The patient reports a family history of skin cancer, immunosuppression, and a personal history of skin cancer. The patient says their skin reddens painfully with sun exposure: 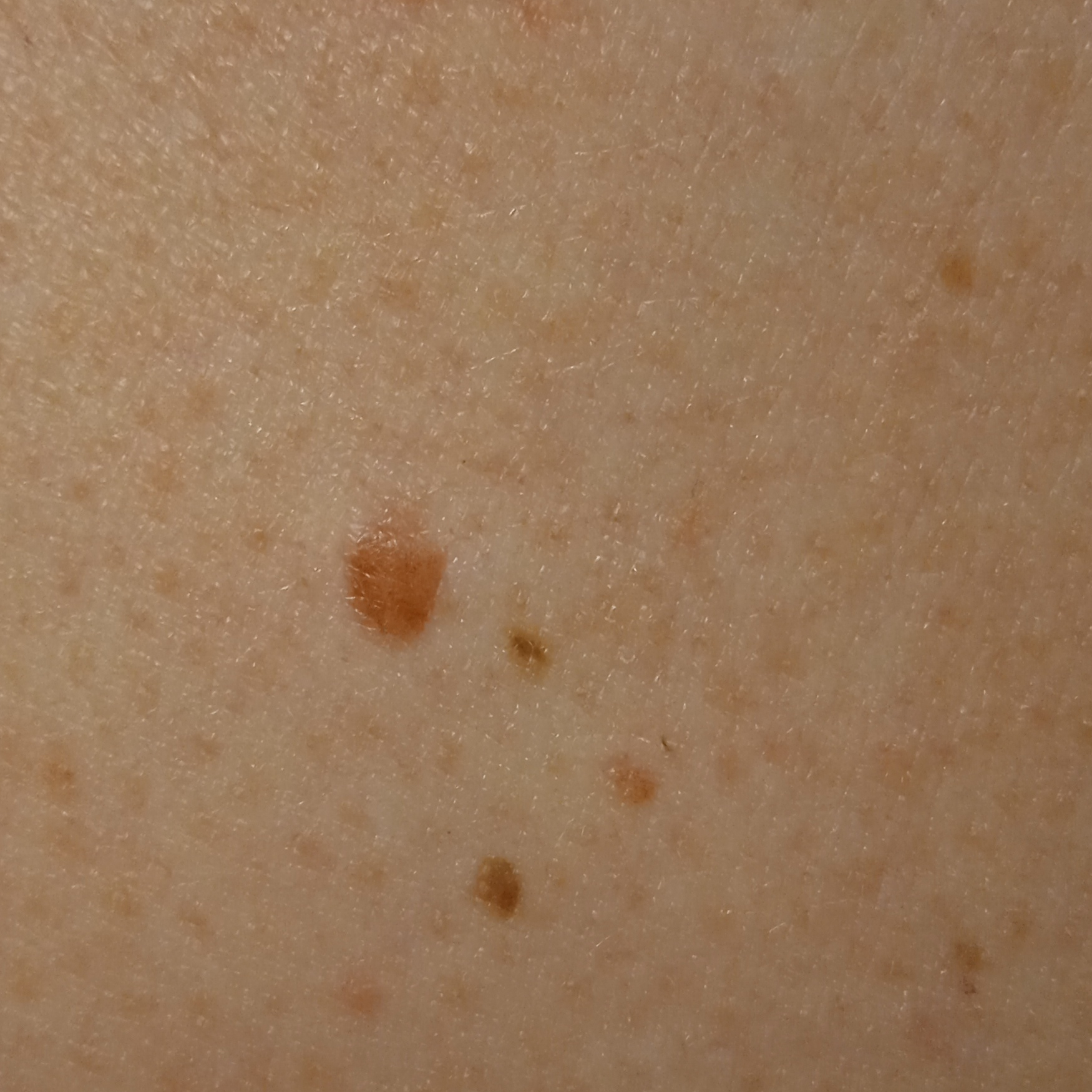Located on the back. The lesion is about 4.4 mm across. The dermatologists' assessment was a melanocytic nevus.